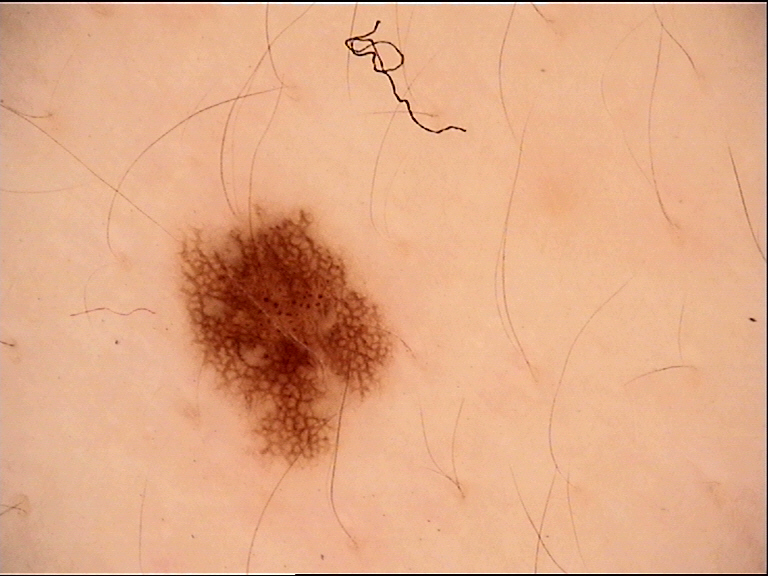| feature | finding |
|---|---|
| label | dysplastic junctional nevus (expert consensus) |